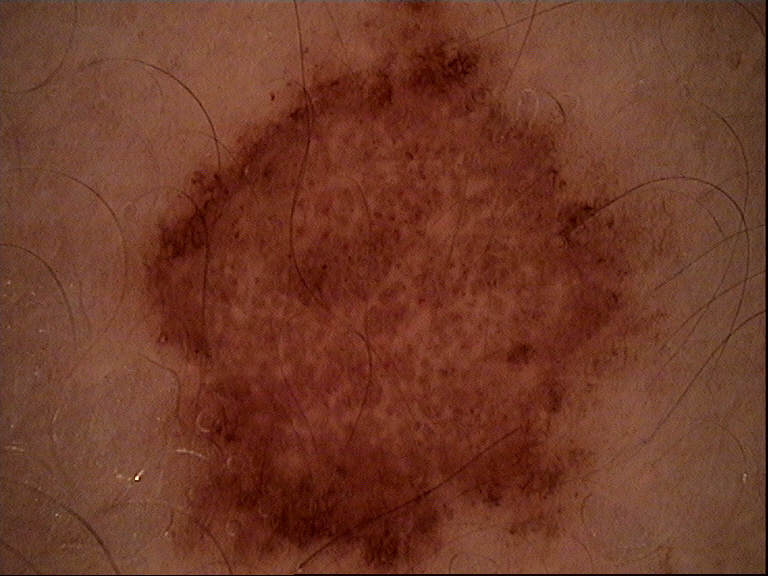Conclusion: The diagnosis was a dysplastic junctional nevus.